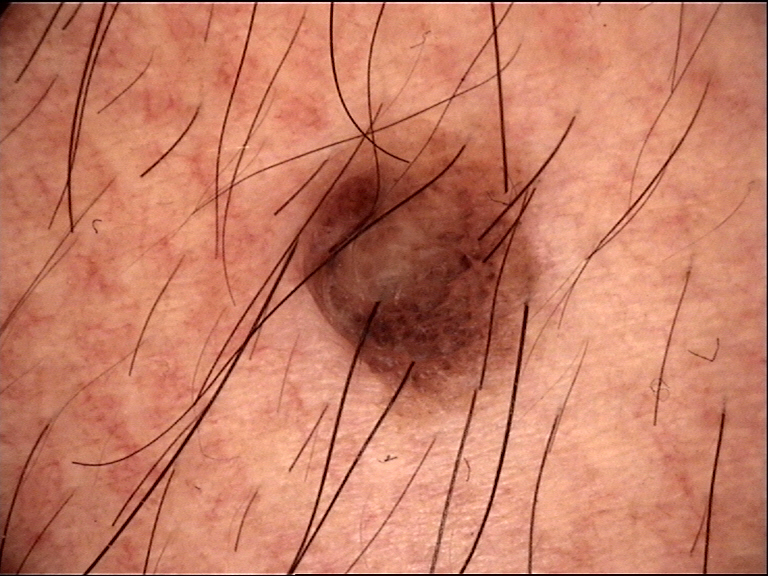image=dermatoscopy | label=compound nevus (expert consensus).